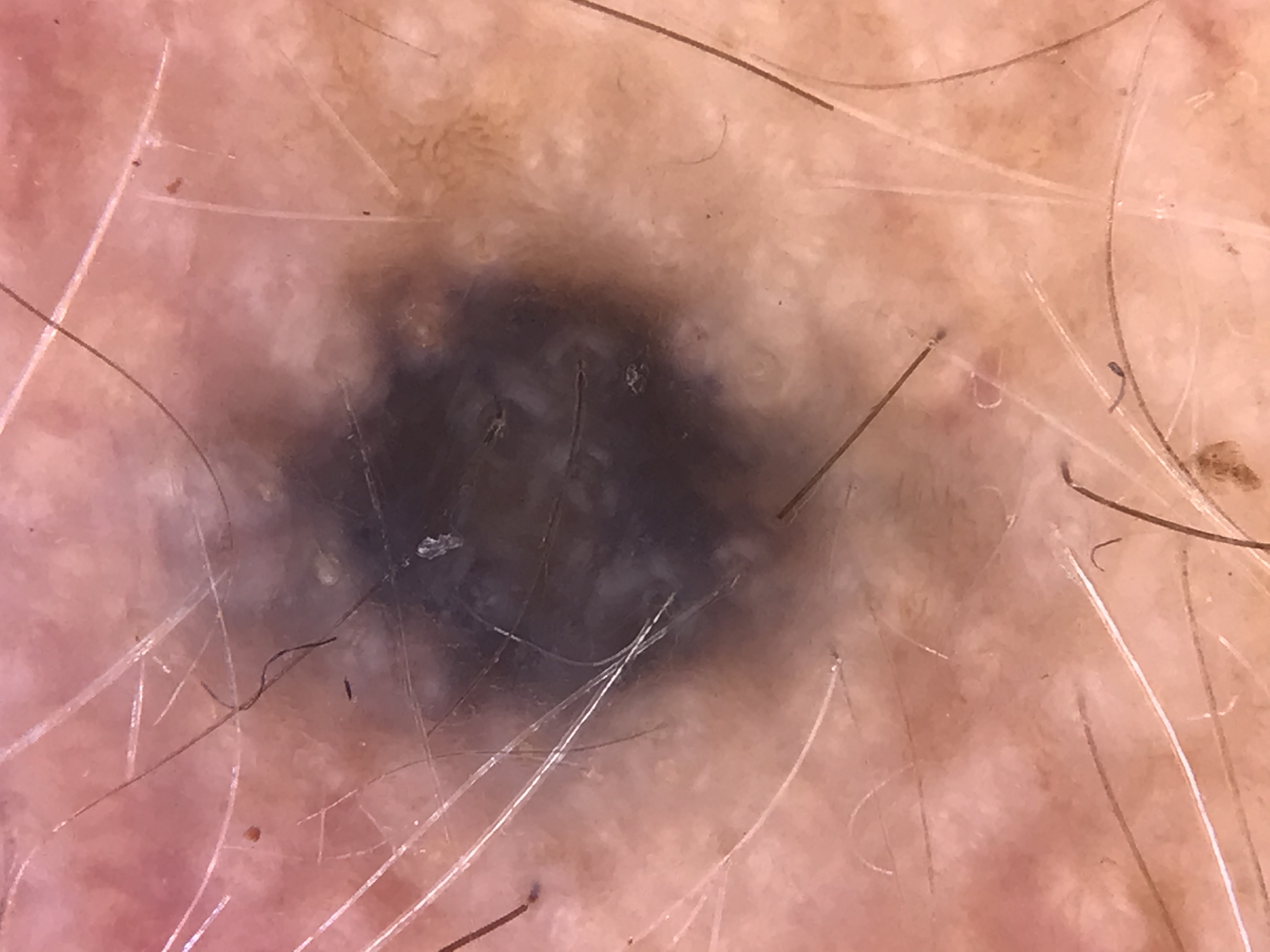{"image": "dermoscopy", "diagnosis": {"name": "blue nevus", "code": "bdb", "malignancy": "benign", "super_class": "melanocytic", "confirmation": "expert consensus"}}